History notes prior malignancy (patient or family). Fitzpatrick I. A male patient aged 80. A smartphone photograph of a skin lesion.
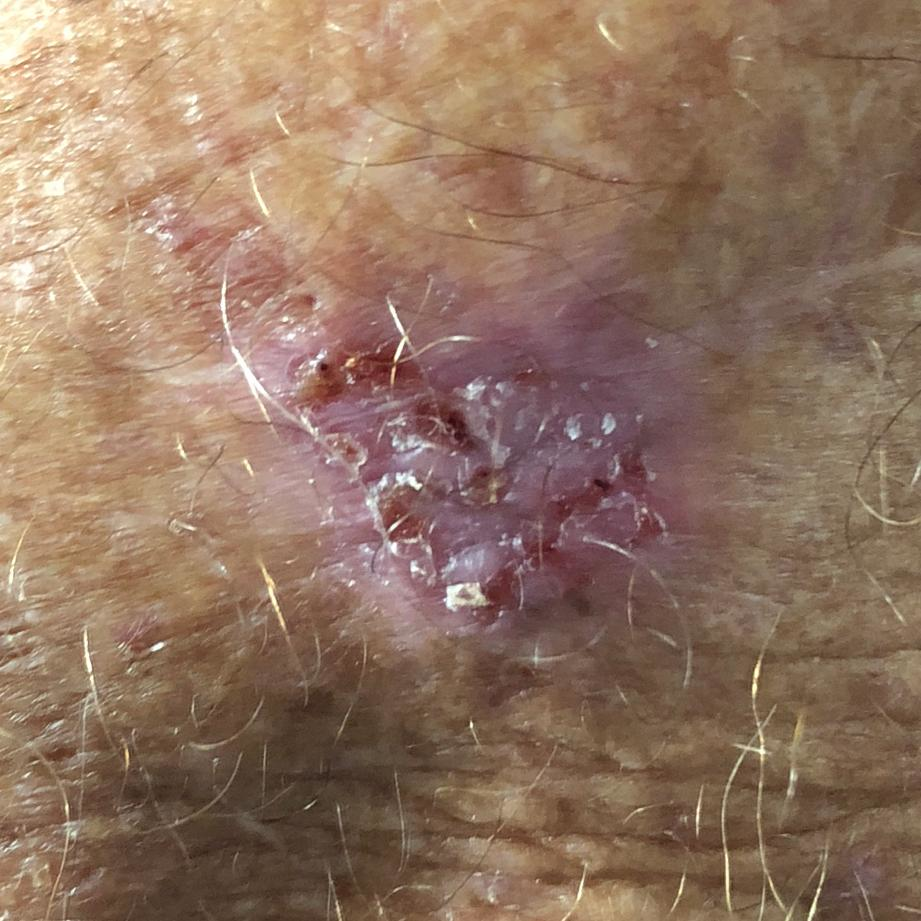The lesion is located on an arm.
The lesion is roughly 12 by 10 mm.
Confirmed on histopathology as a basal cell carcinoma.